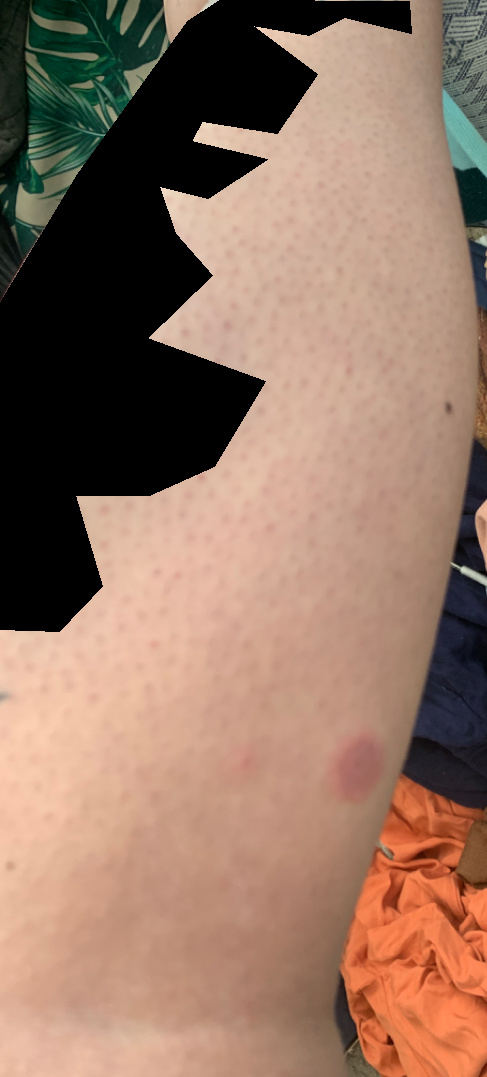– body site — leg
– subject — female, age 18–29
– shot type — at a distance
– symptoms — none reported
– present for — one to four weeks
– differential — Eczema (favored); Psoriasis (possible); Tinea (possible); Pityriasis rosea (less likely)